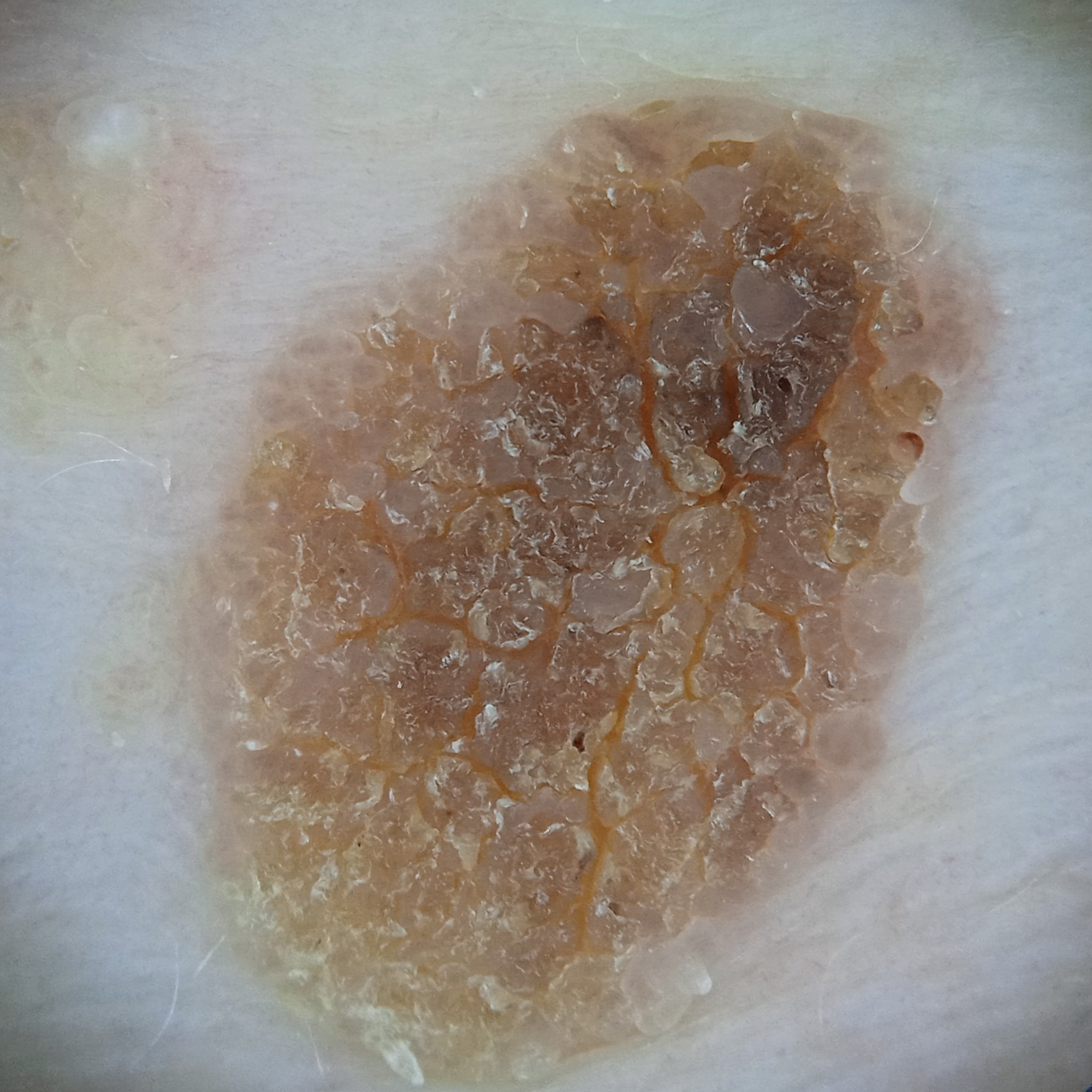subject: female, aged 81
sun reaction: skin reddens painfully with sun exposure
nevus count: a moderate number of melanocytic nevi
image: dermoscopy
referral: research study (no referral diagnosis)
site: the torso
size: 12.2 mm
assessment: seborrheic keratosis (dermatologist consensus)